A dermatoscopic image of a skin lesion.
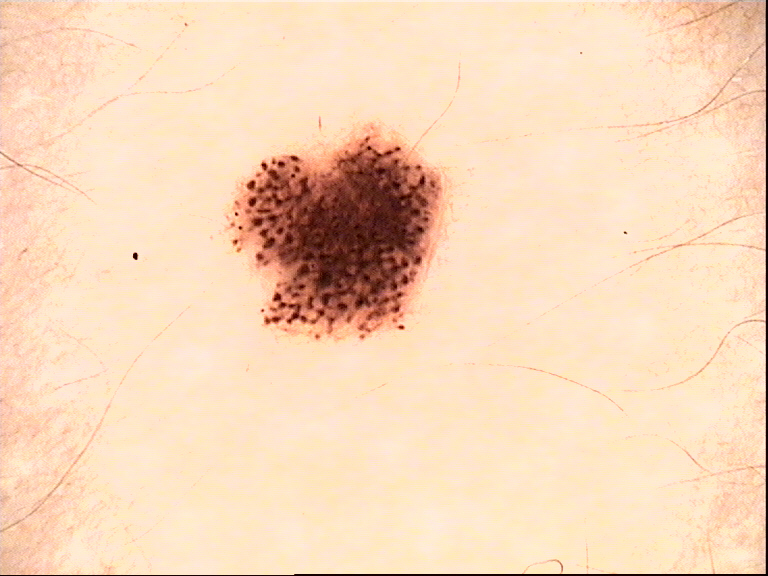Q: What is this lesion?
A: compound nevus (expert consensus)